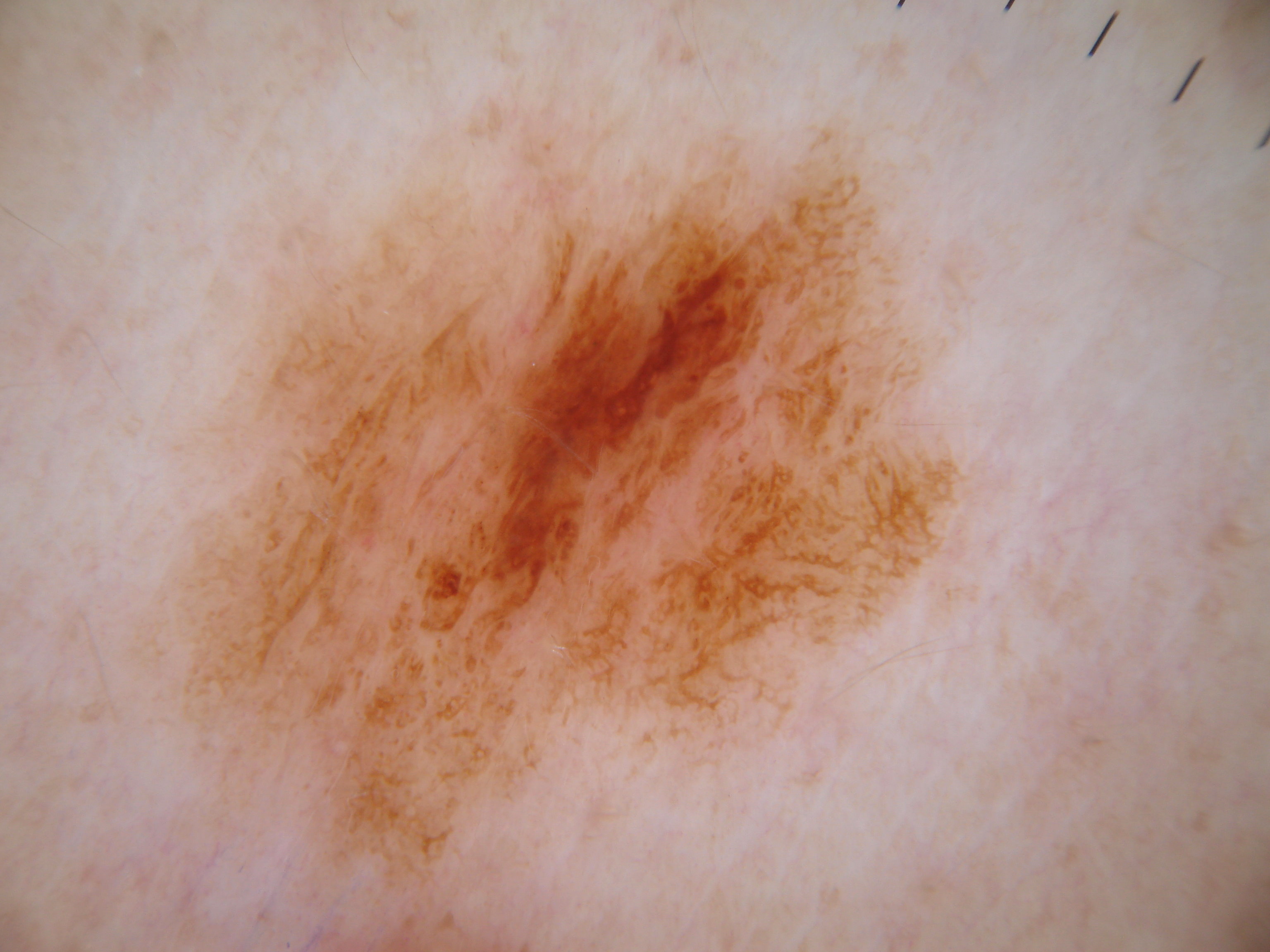| feature | finding |
|---|---|
| modality | dermatoscopic image of a skin lesion |
| dermoscopic findings | globules and pigment network |
| location | box(82, 13, 996, 932) |
| extent | large |
| impression | a melanocytic nevus, a benign skin lesion |